Dermoscopy of a skin lesion; a female patient, in their mid-60s:
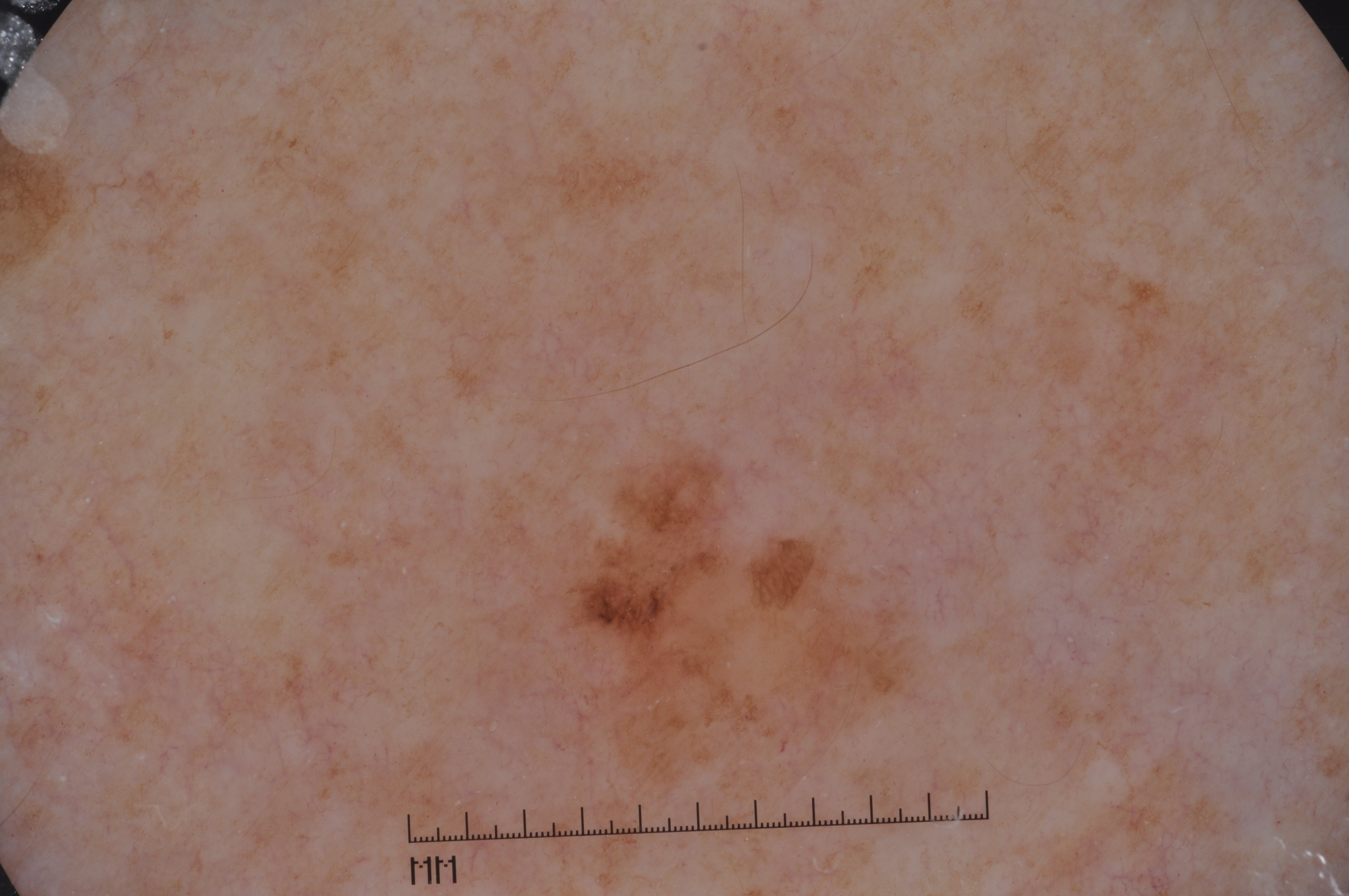lesion extent — moderate
location — <bbox>549, 450, 921, 832</bbox>
dermoscopic pattern — pigment network; absent: milia-like cysts, negative network, and streaks
diagnosis — a melanocytic nevus